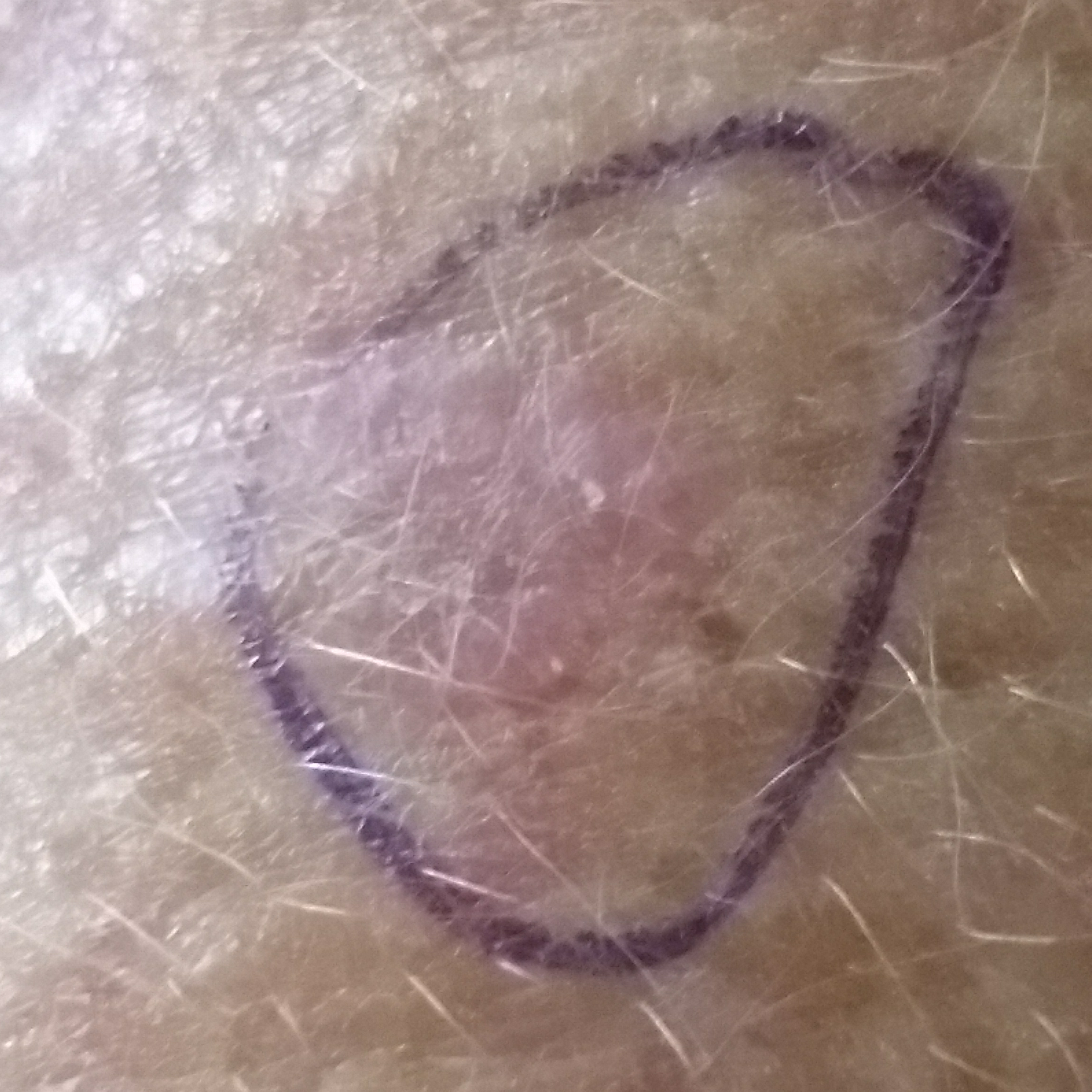A clinical photograph showing a skin lesion. A female subject in their 50s. The lesion is located on a forearm. The diagnostic impression was an actinic keratosis.